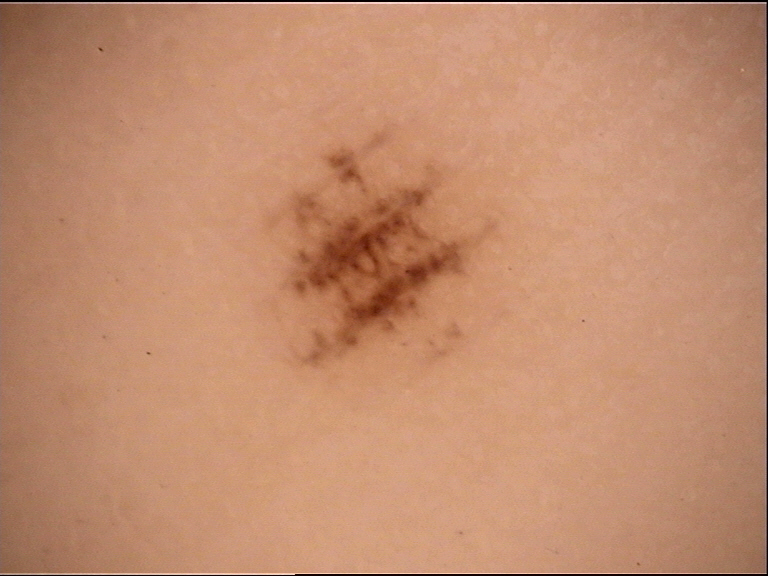imaging = dermoscopy; class = acral junctional nevus (expert consensus).